Reported lesion symptoms include burning and pain. Self-categorized by the patient as a rash. The photo was captured at an angle. Texture is reported as flat. The lesion involves the arm. The patient notes the condition has been present for about one day:
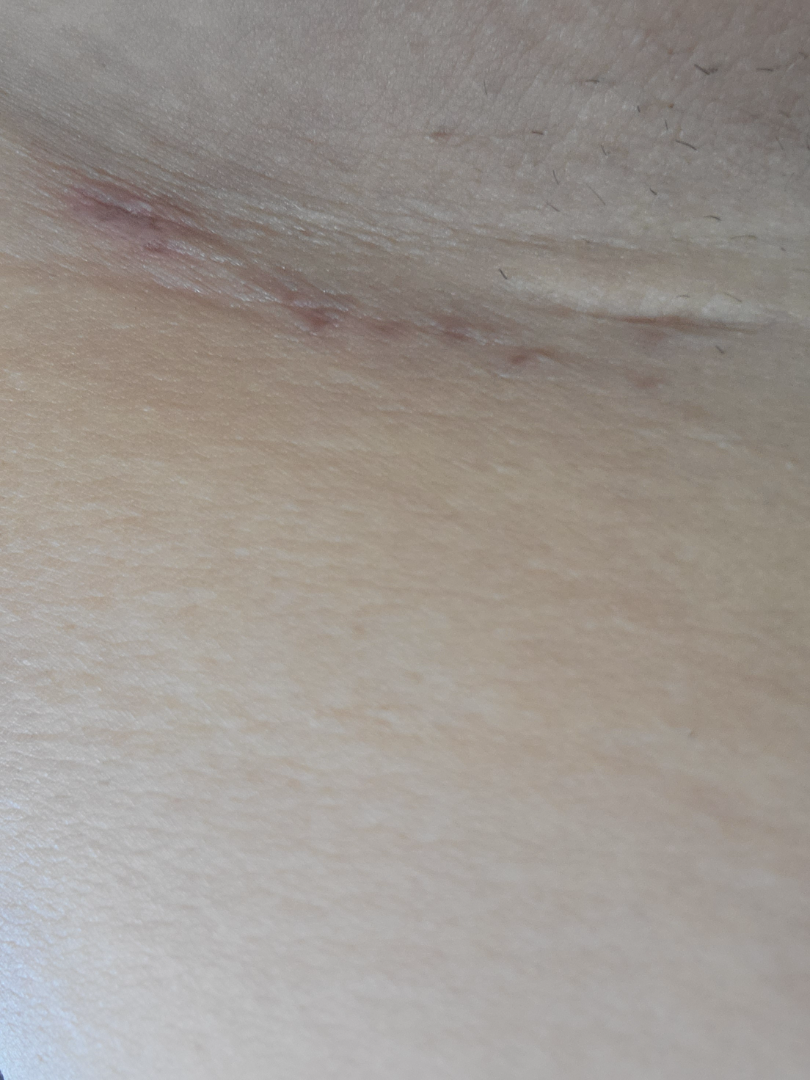Q: What conditions are considered?
A: most consistent with Hidradenitis; also on the differential is Abscess